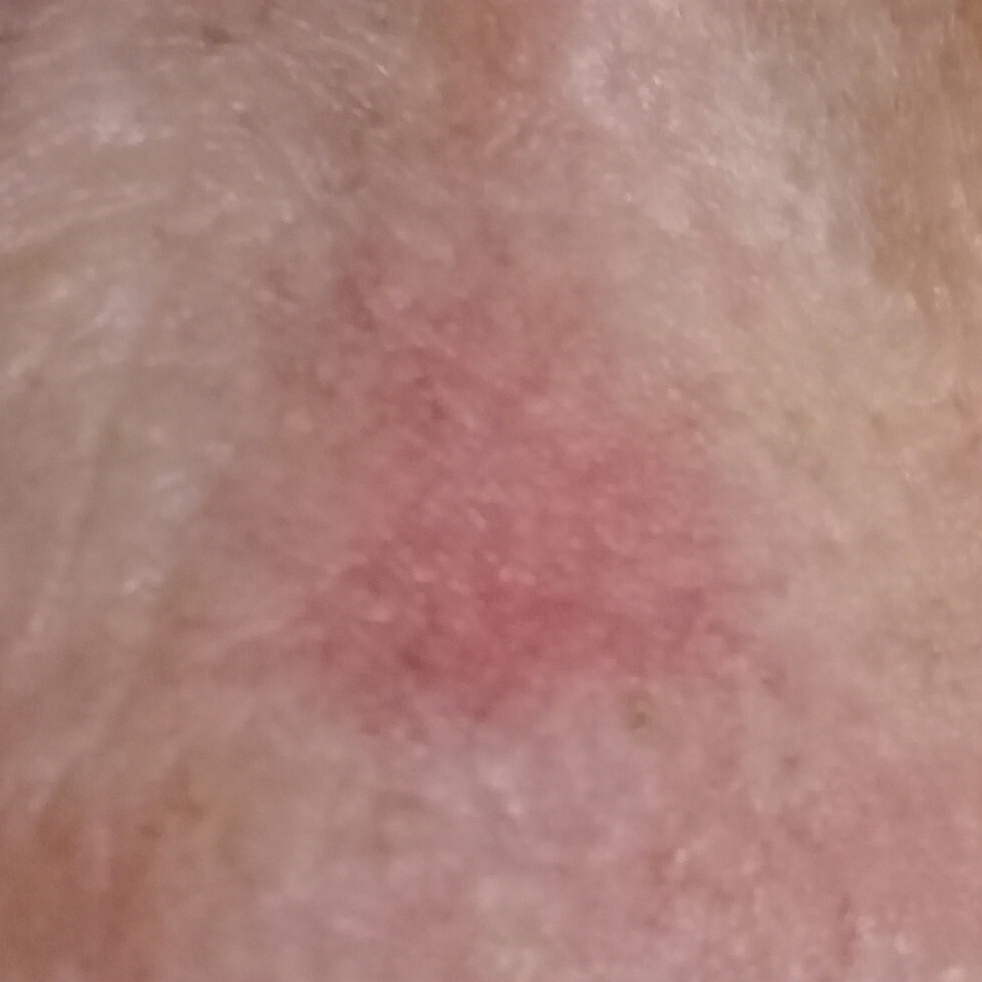imaging = smartphone clinical photo, patient = in their mid-60s, body site = the face, patient-reported symptoms = no bleeding, impression = actinic keratosis (clinical consensus).